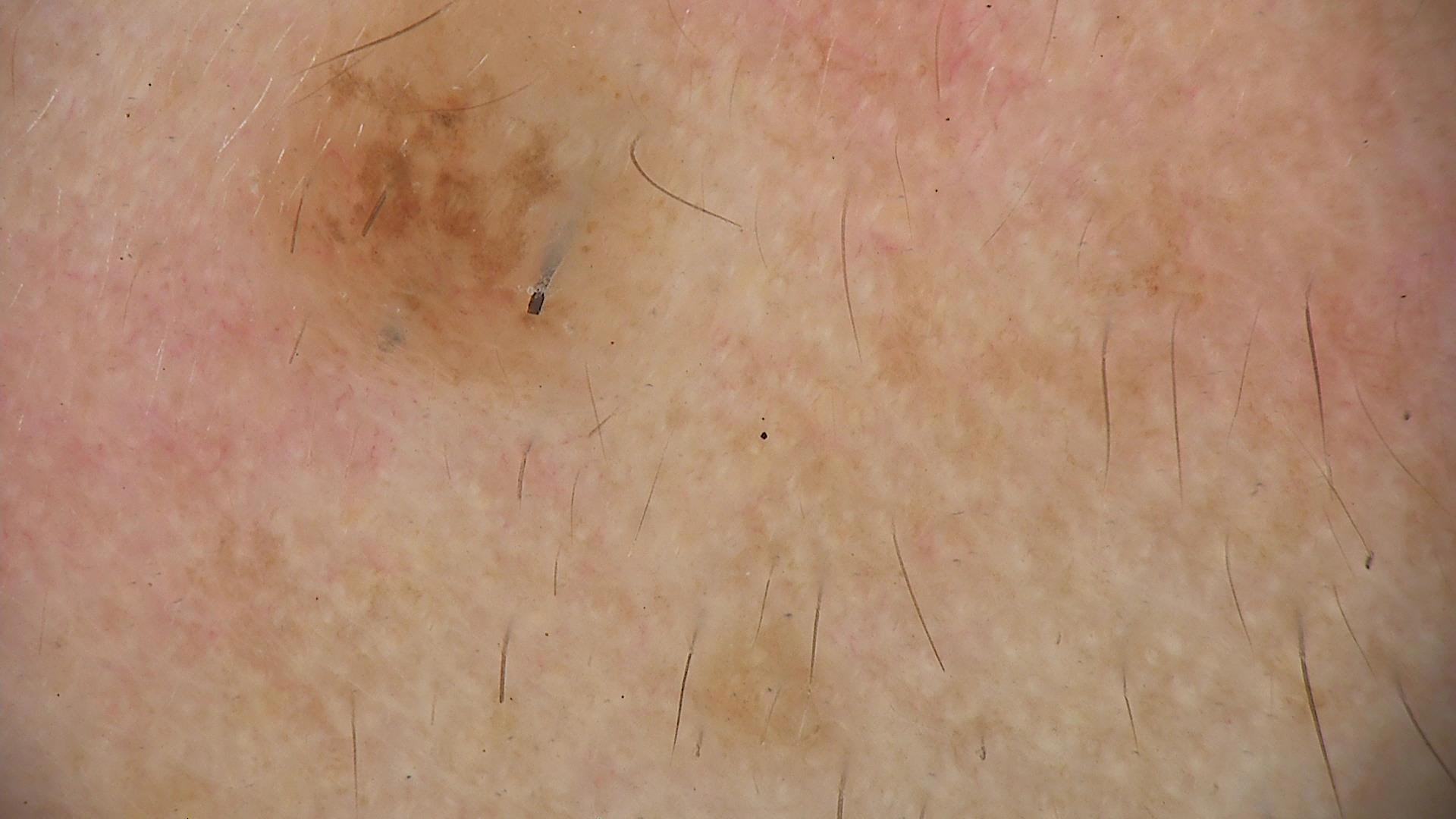A dermoscopic photograph of a skin lesion.
The diagnostic label was a banal lesion — a compound nevus.